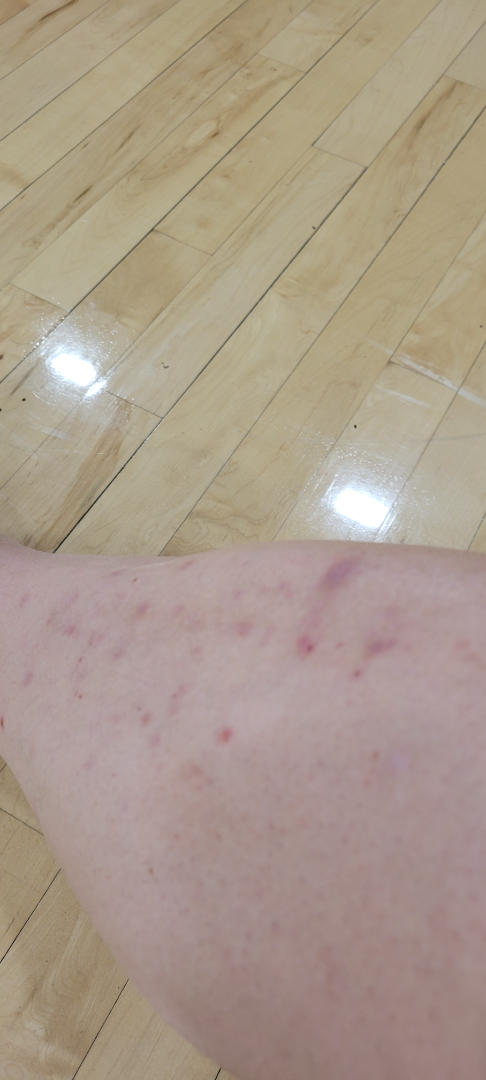| field | value |
|---|---|
| affected area | leg and top or side of the foot |
| lesion texture | raised or bumpy |
| patient | male, age 40–49 |
| framing | at an angle |
| patient's own categorization | a rash |
| symptoms | itching and bothersome appearance |
| clinical impression | most consistent with Folliculitis; also raised was Insect Bite; a more distant consideration is Eczema |